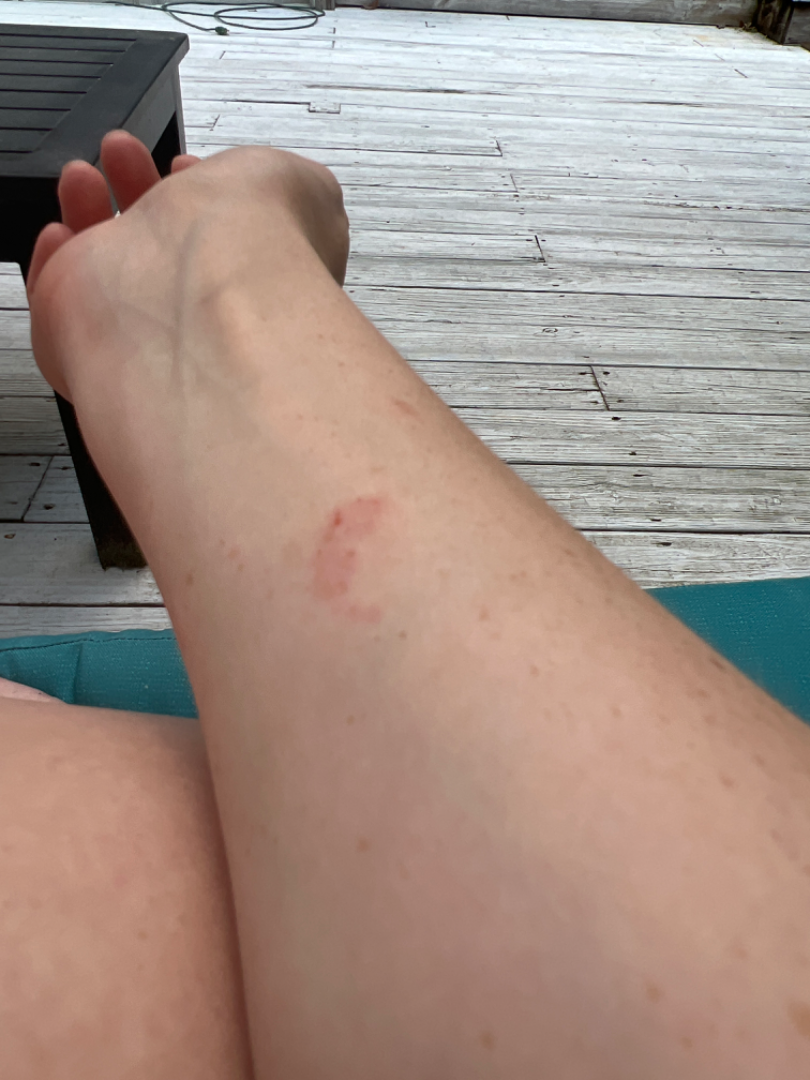The reviewer was unable to grade this case for skin condition.